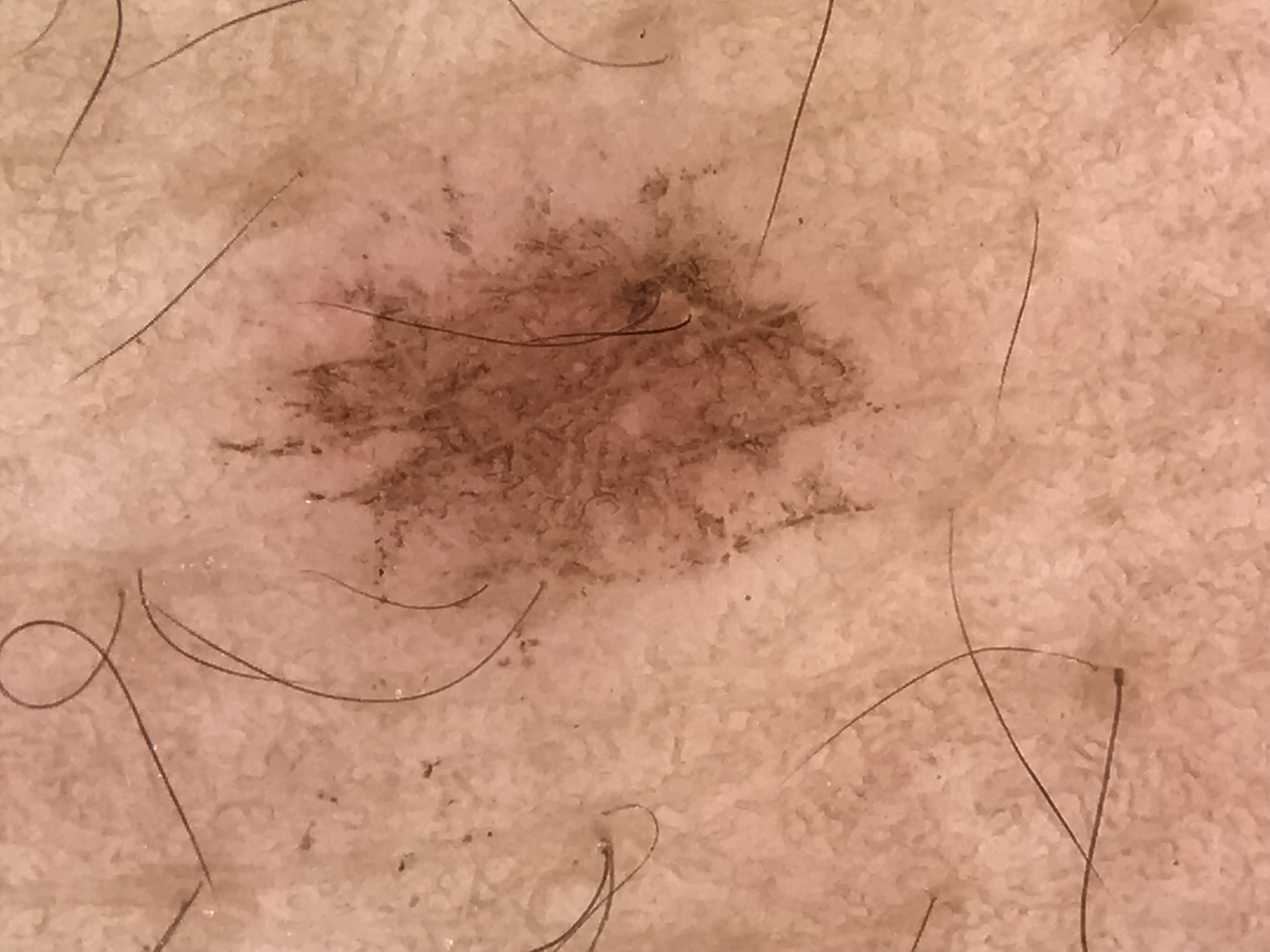Impression: Labeled as a lentigo simplex.